The patient is a male in their 70s · a dermoscopy image of a single skin lesion:
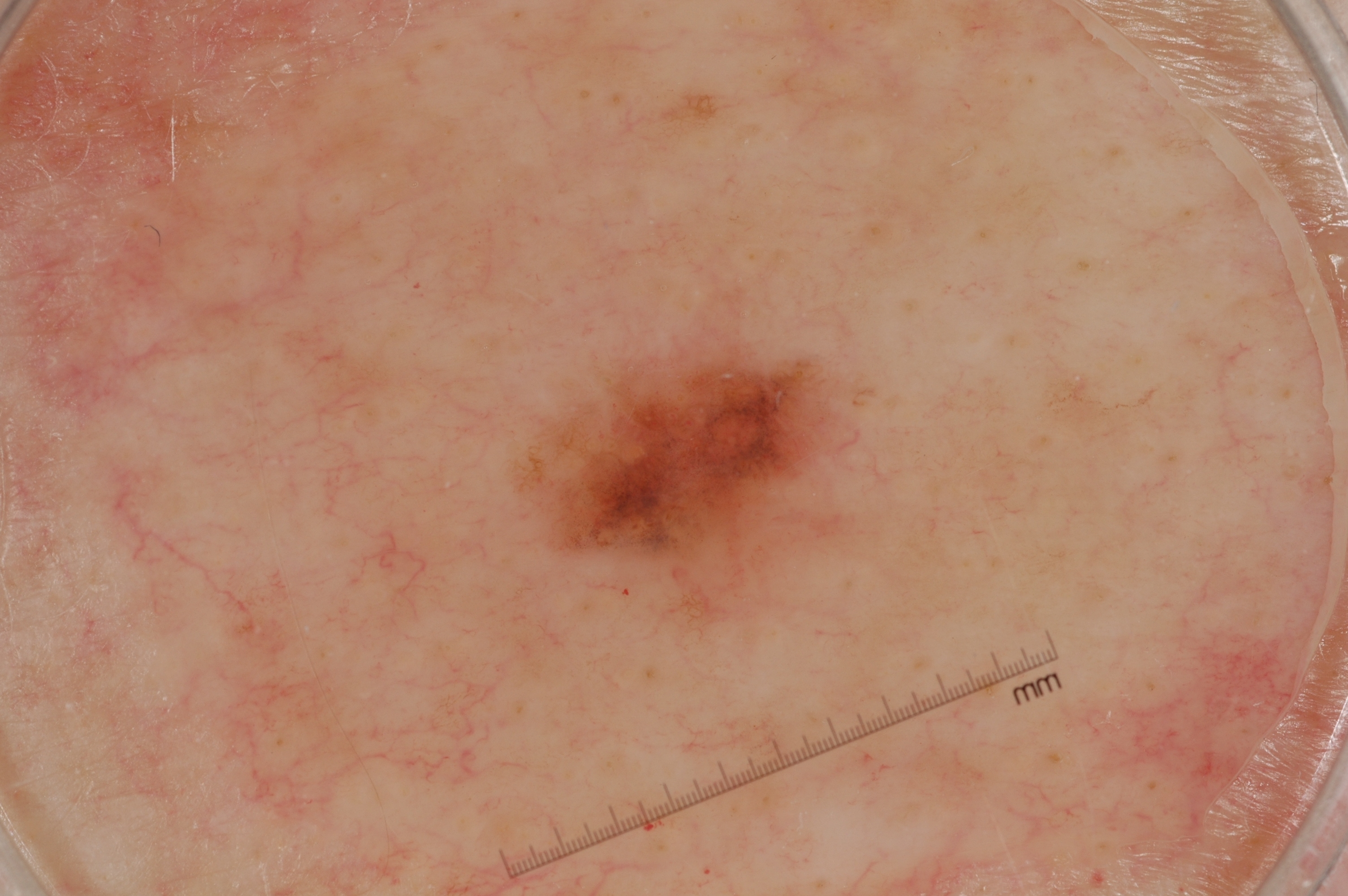The lesion covers approximately 5% of the dermoscopic field.
As (left, top, right, bottom), the lesion occupies the region [527, 343, 832, 623].
Dermoscopy demonstrates milia-like cysts; no negative network, streaks, or pigment network.
Histopathologically confirmed as a melanoma, a skin cancer.